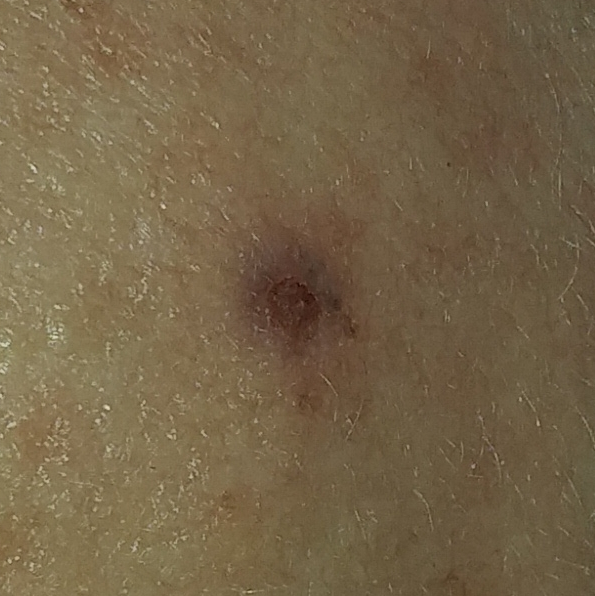- anatomic site · the face
- symptoms · elevation, itching, bleeding / no pain
- diagnostic label · basal cell carcinoma (biopsy-proven)